Dermoscopy of a skin lesion:
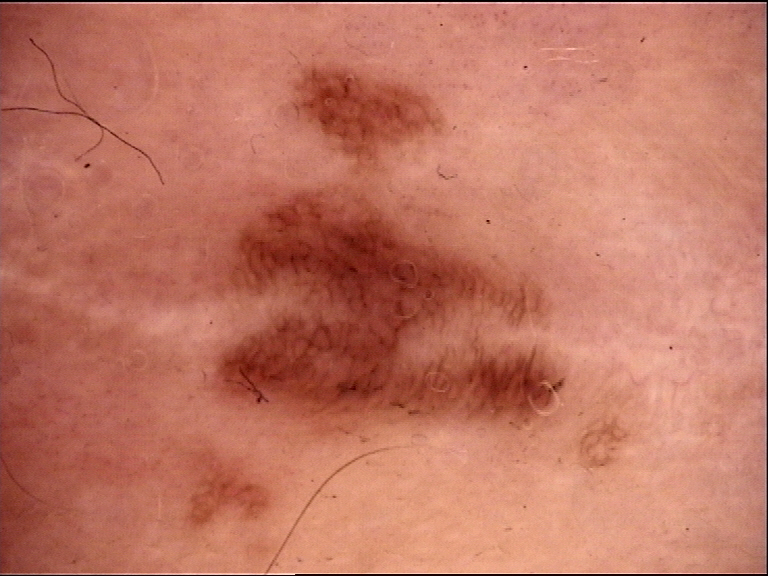The diagnostic label was a dysplastic lesion — a recurrent nevus.